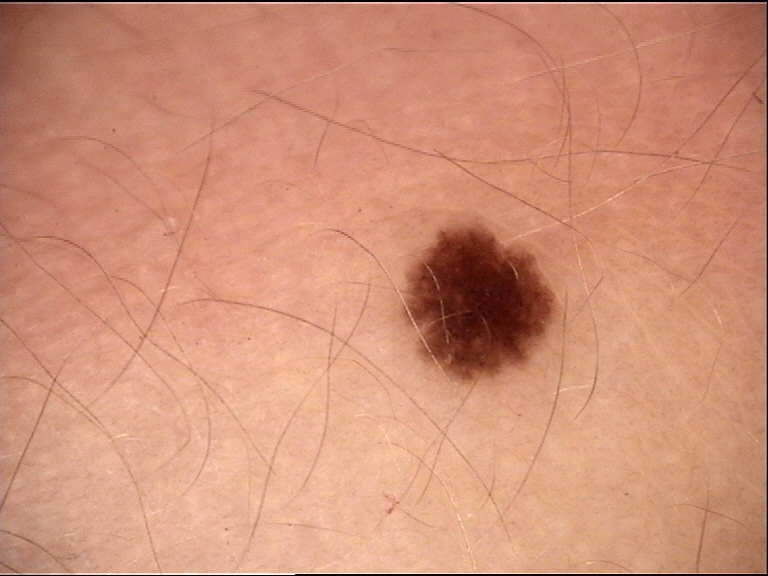subtype: banal | diagnosis: junctional nevus (expert consensus).